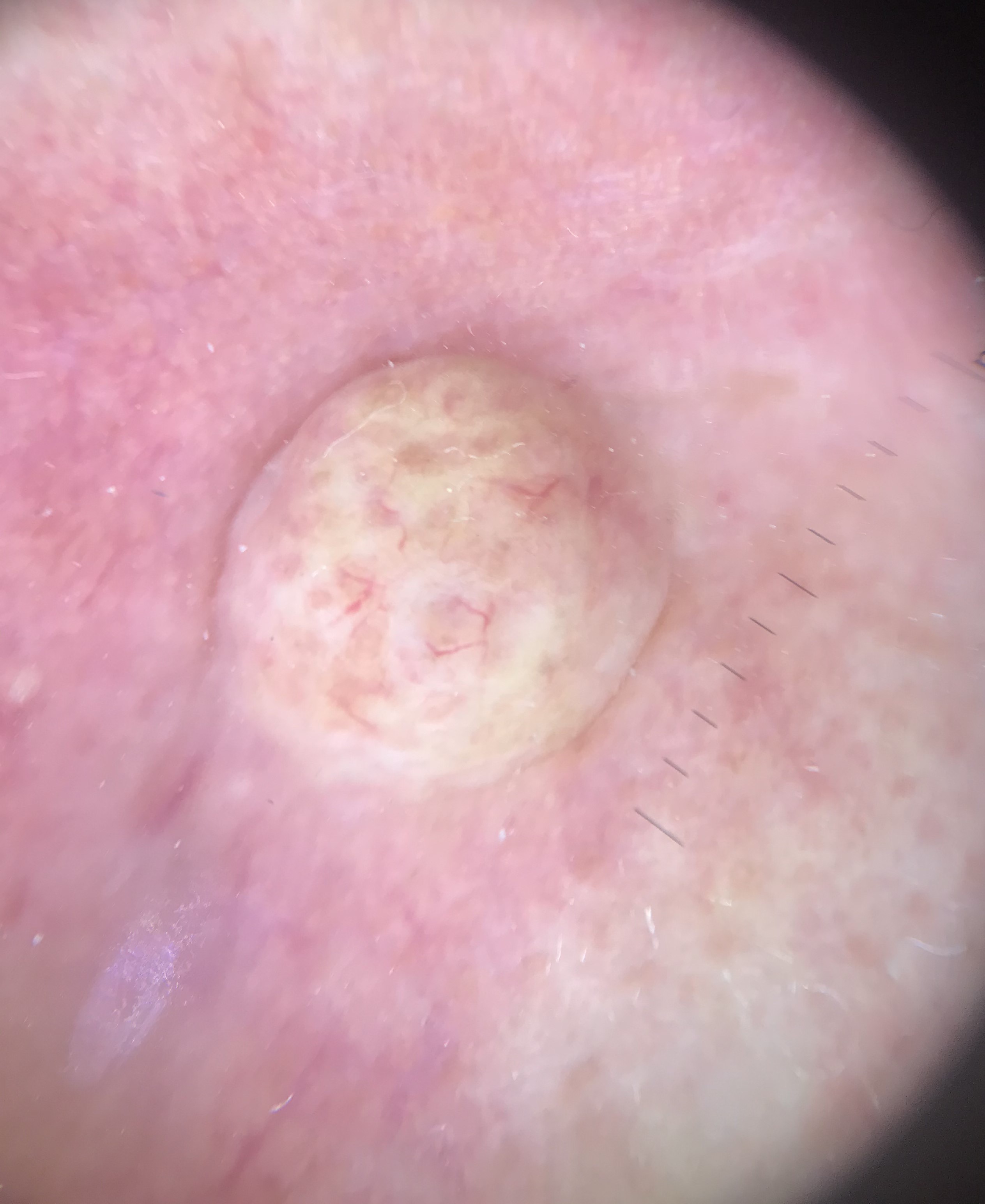A dermatoscopic image of a skin lesion. Labeled as a banal lesion — a dermal nevus.